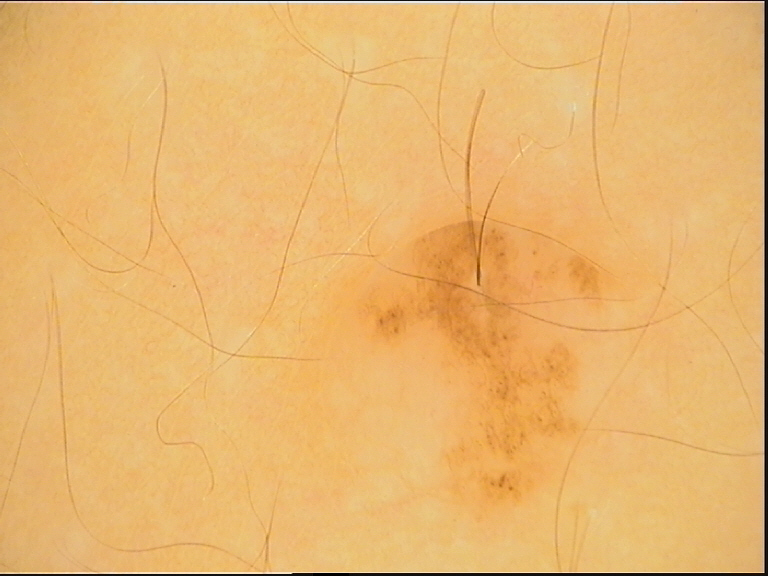- label: dermal nevus (expert consensus)